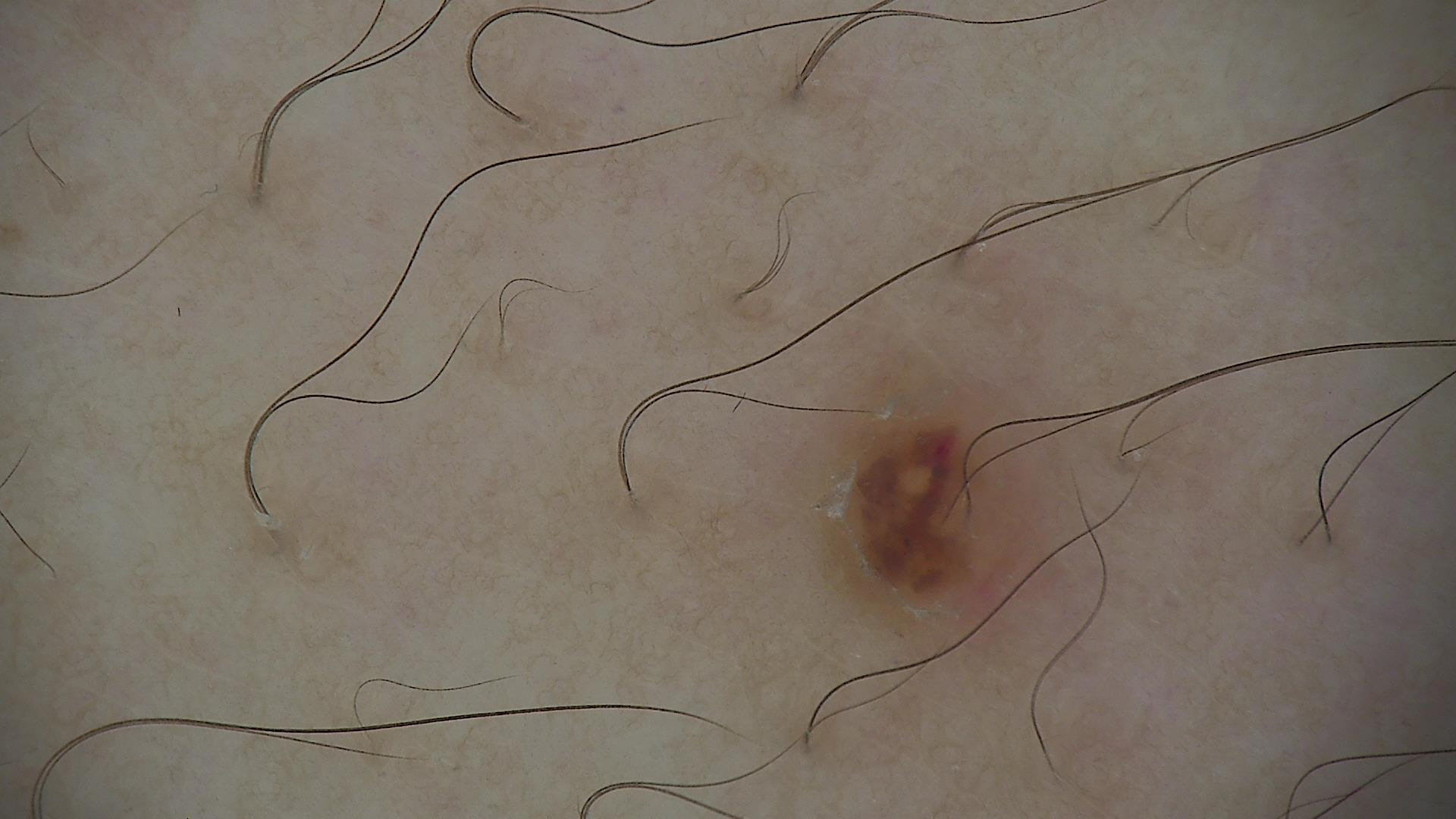A dermoscopic photograph of a skin lesion. Diagnosed as a benign lesion — a dysplastic junctional nevus.